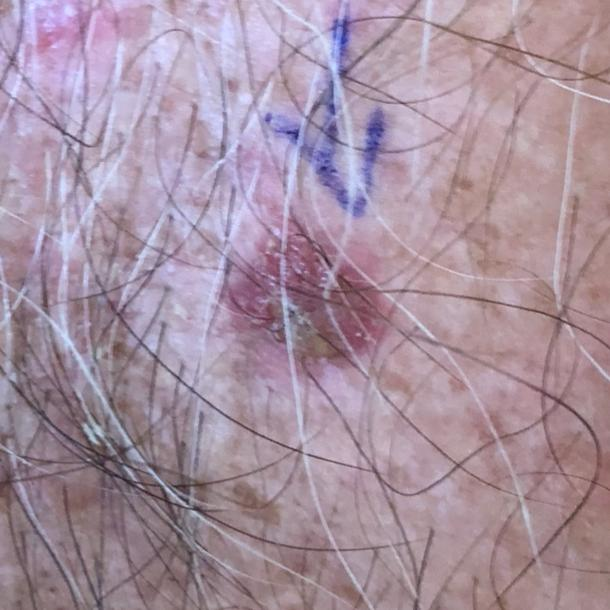Q: What is the patient's skin type?
A: II
Q: What are the relevant risk factors?
A: alcohol use, prior malignancy (patient or family), no pesticide exposure
Q: Who is the patient?
A: male, aged 78
Q: What is the anatomic site?
A: the chest
Q: Lesion size?
A: 11 × 10 mm
Q: What does the patient describe?
A: pain, growth, bleeding, itching
Q: What did the workup show?
A: basal cell carcinoma (biopsy-proven)